The patient indicates itching and enlargement, the lesion is described as raised or bumpy, the photograph was taken at an angle, the arm is involved, self-categorized by the patient as a rash.
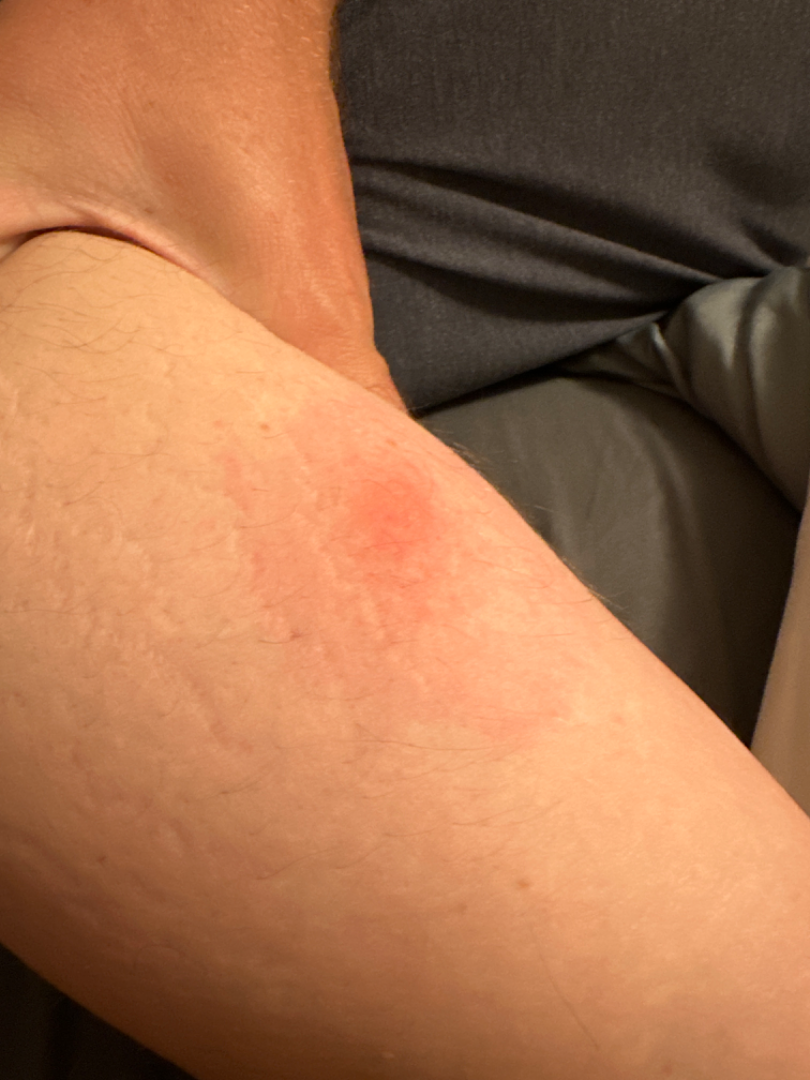On photographic review: most consistent with Erythema migrans; also on the differential is Cellulitis; an alternative is Insect Bite.